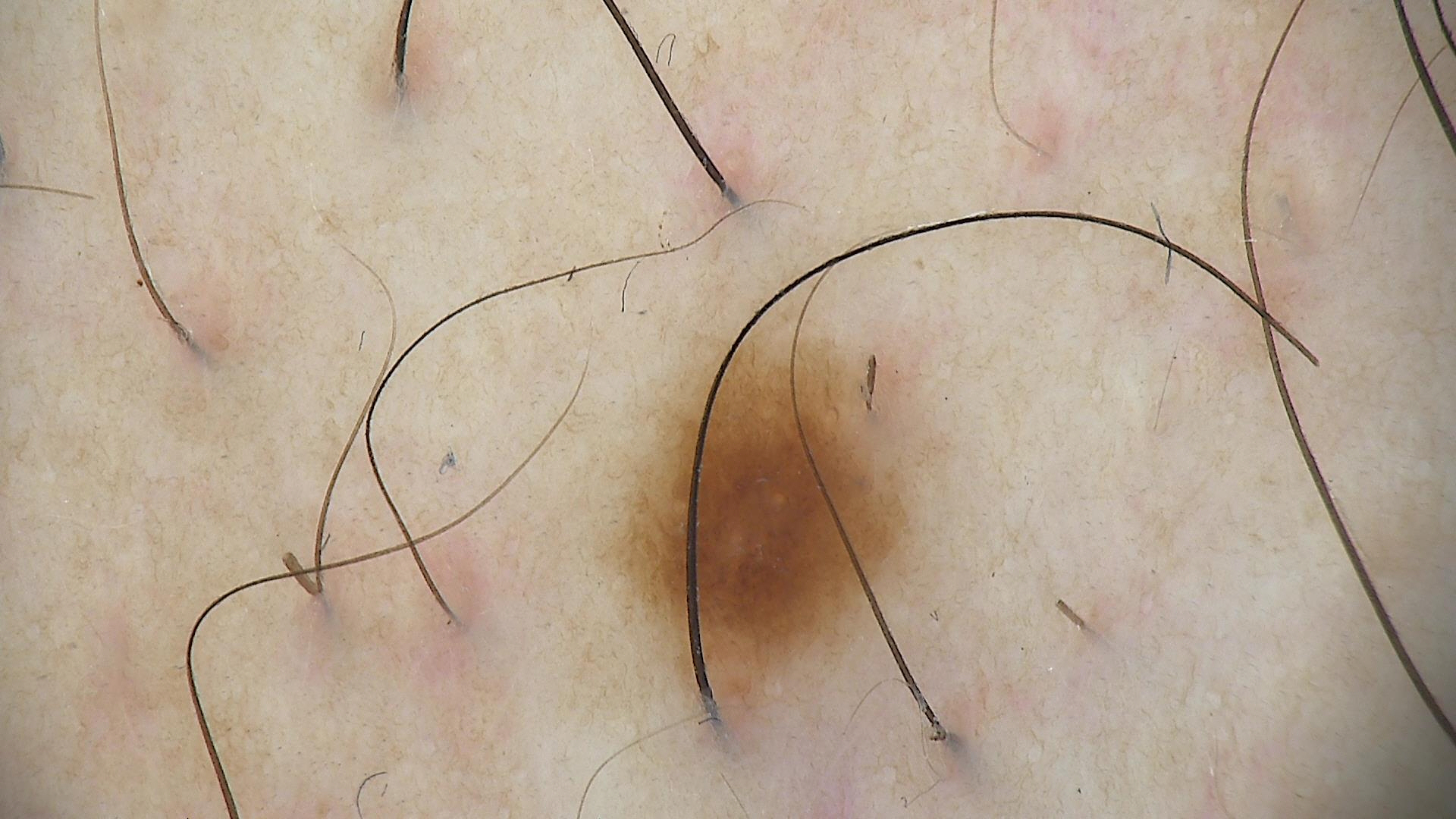Findings:
• diagnosis — dysplastic junctional nevus (expert consensus)